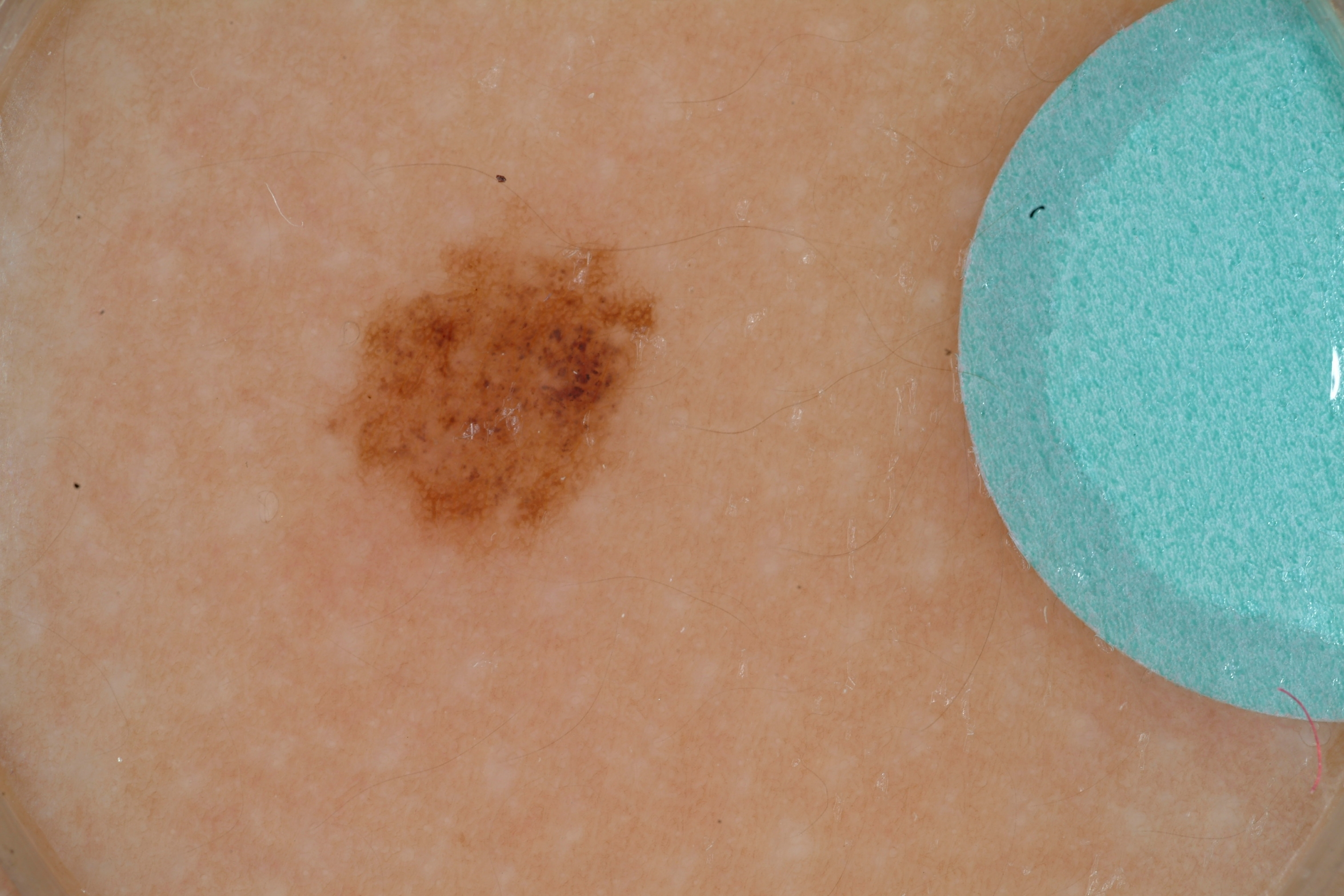{"image": {"modality": "dermoscopy"}, "patient": {"sex": "female", "age_approx": 15}, "dermoscopic_features": {"present": ["globules", "pigment network"], "absent": ["milia-like cysts", "streaks", "negative network"]}, "lesion_location": {"bbox_xyxy": [311, 191, 671, 575]}, "lesion_extent": "small", "diagnosis": {"name": "melanocytic nevus", "malignancy": "benign", "lineage": "melanocytic", "provenance": "clinical"}}